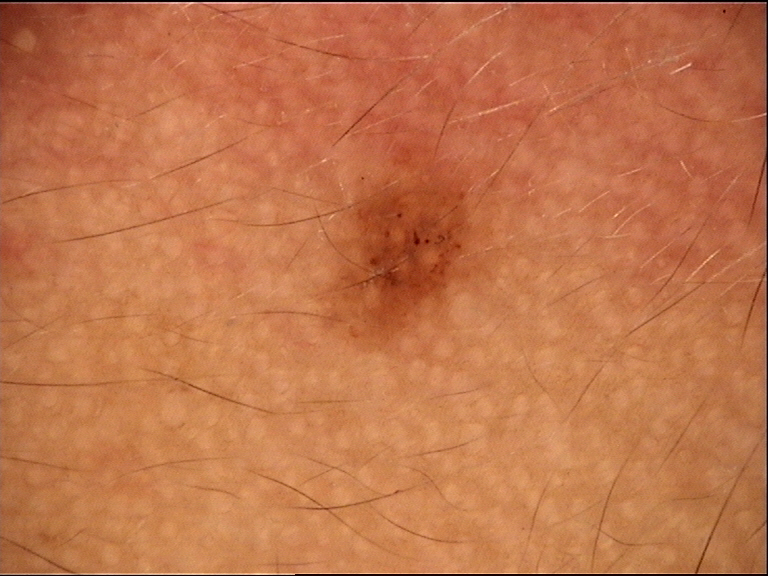classification: compound, banal; assessment: Miescher nevus (expert consensus).